The patient is a male aged 18–29. This image was taken at a distance. The lesion involves the front of the torso, leg, top or side of the foot, arm and back of the hand — 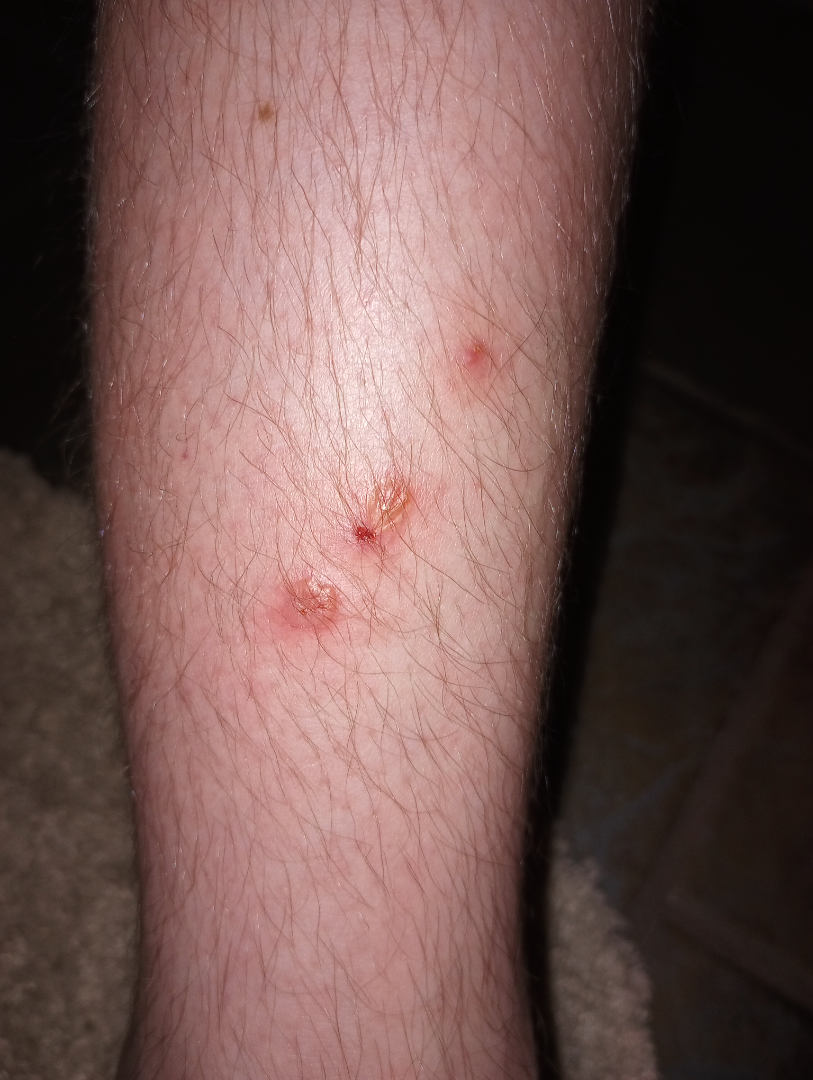Assessment:
The differential includes Allergic Contact Dermatitis and Irritant Contact Dermatitis, with no clear leading consideration.